This is a close-up image, located on the leg:
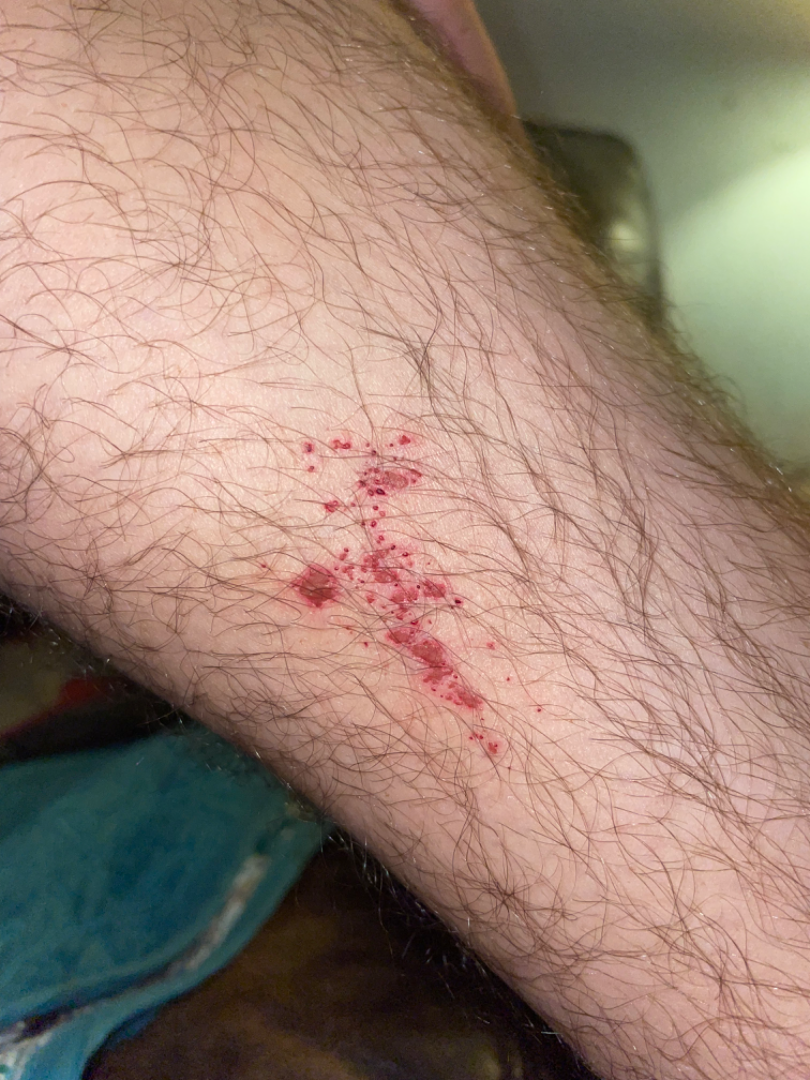Q: What is the dermatologist's impression?
A: the impression was split between Purpura and Angiokeratoma of skin